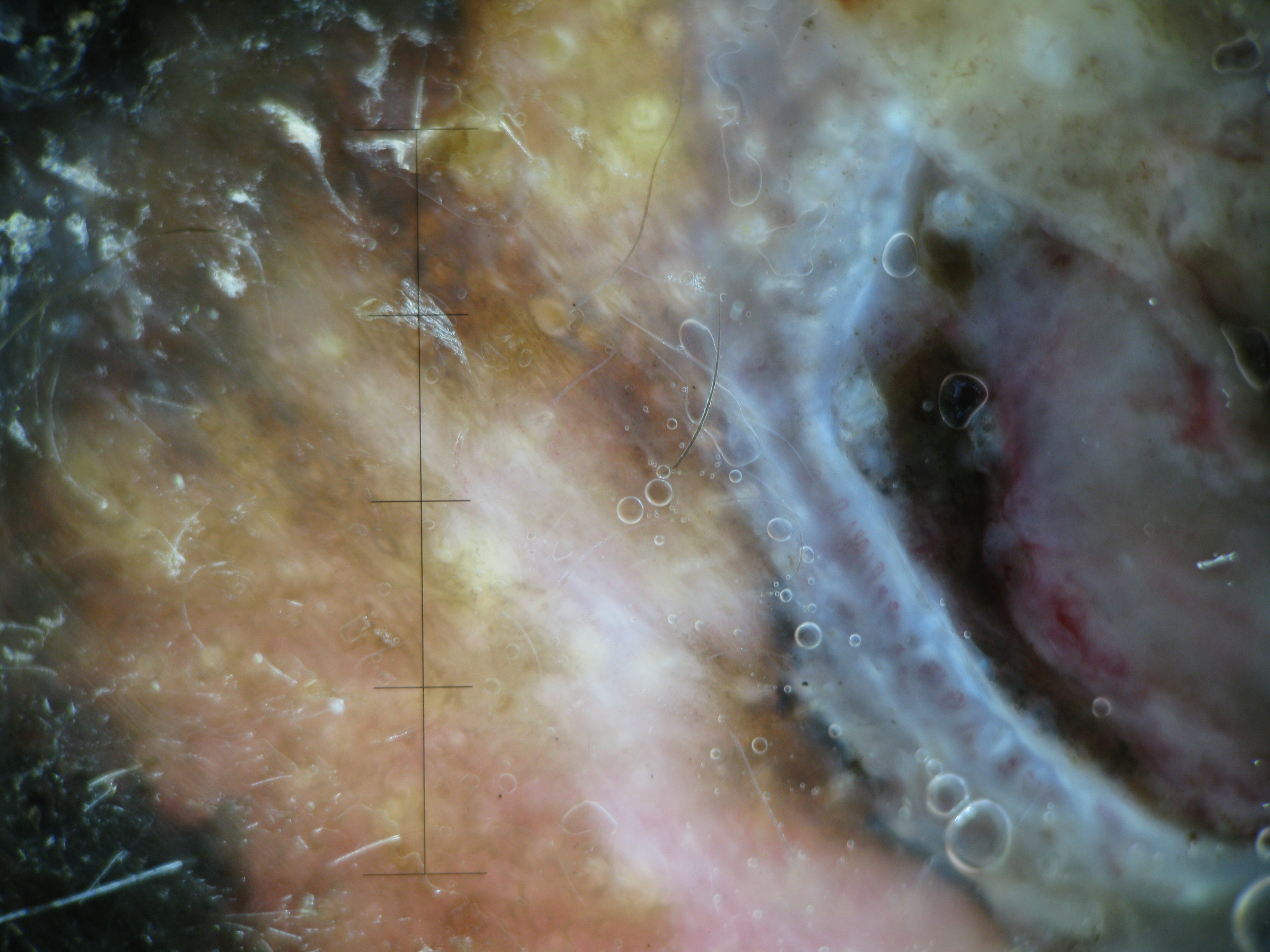A dermoscopic image of a skin lesion. Histopathologically confirmed as a malignancy — a lentigo maligna melanoma.